This image was taken at a distance · the contributor is a female aged 50–59 · present for less than one week · the affected area is the front of the torso and back of the torso · the patient indicates the lesion is raised or bumpy · Fitzpatrick skin type II · reported lesion symptoms include itching, enlargement and bothersome appearance.
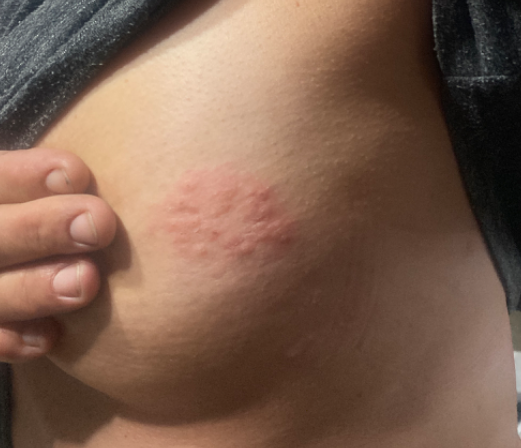The reviewing dermatologist was unable to assign a differential diagnosis from the image.